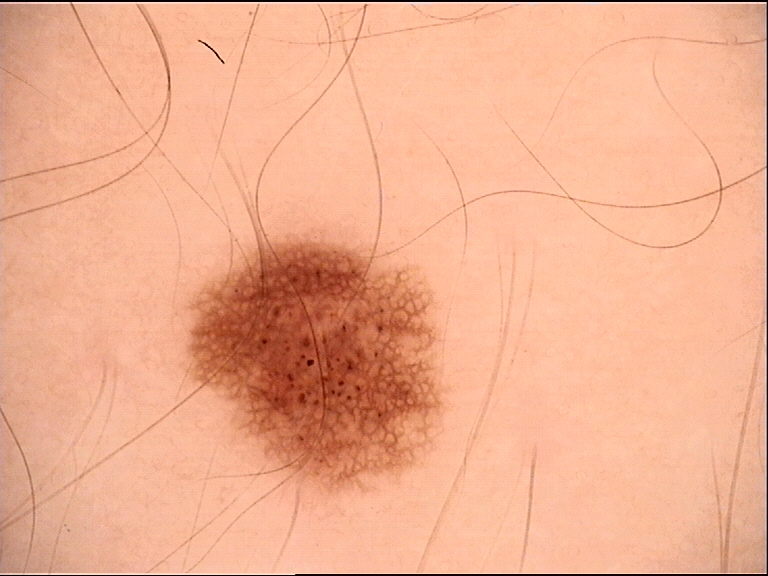A dermoscopy image of a single skin lesion.
Labeled as a banal lesion — a junctional nevus.